The patient reports the condition has been present for less than one week · the patient considered this a rash · an image taken at a distance · associated systemic symptoms include joint pain · the lesion is described as flat and rough or flaky — 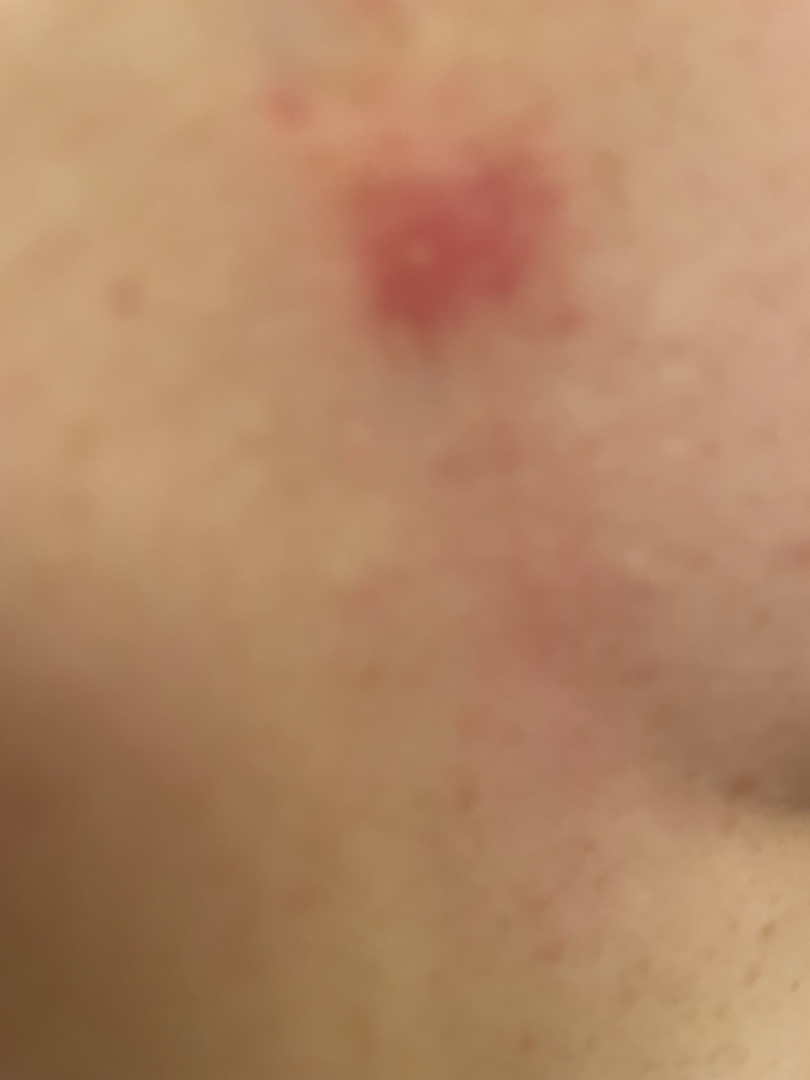assessment = unable to determine